A male subject, aged approximately 70; dermoscopy of a skin lesion:
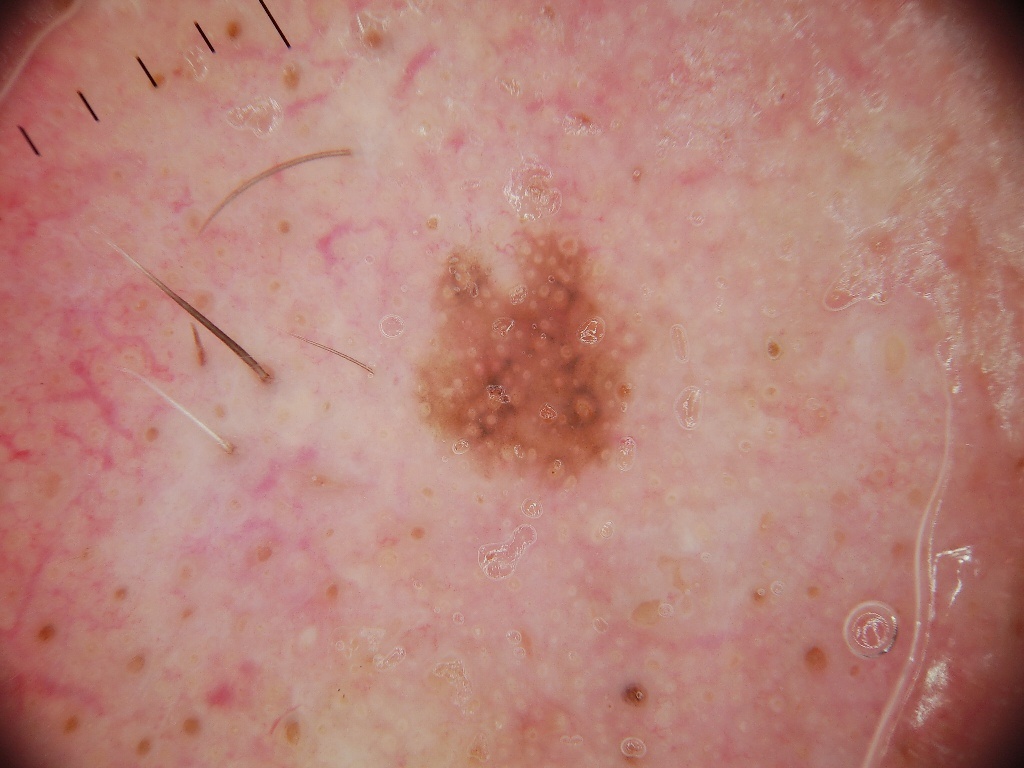Notes:
- lesion location · left=418, top=226, right=646, bottom=489
- absent dermoscopic features · streaks, negative network, pigment network, milia-like cysts, and globules
- diagnosis · a melanoma, a malignant lesion